A female subject, aged 8 to 12; a dermatoscopic image of a skin lesion:
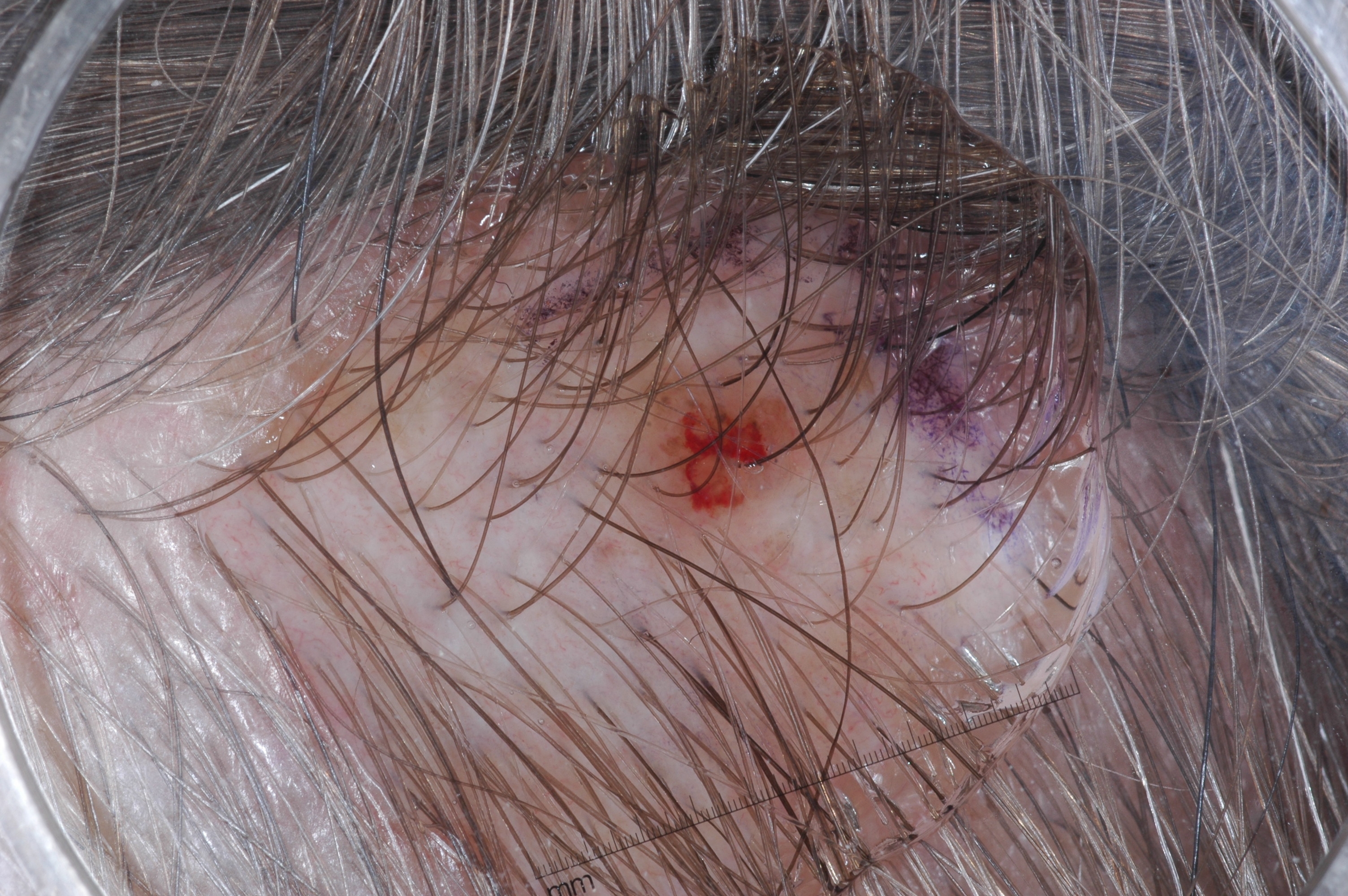| feature | finding |
|---|---|
| extent | small |
| dermoscopic features assessed but absent | pigment network, negative network, milia-like cysts, and streaks |
| location | 603 316 892 583 |
| diagnostic label | a melanocytic nevus, a benign lesion |